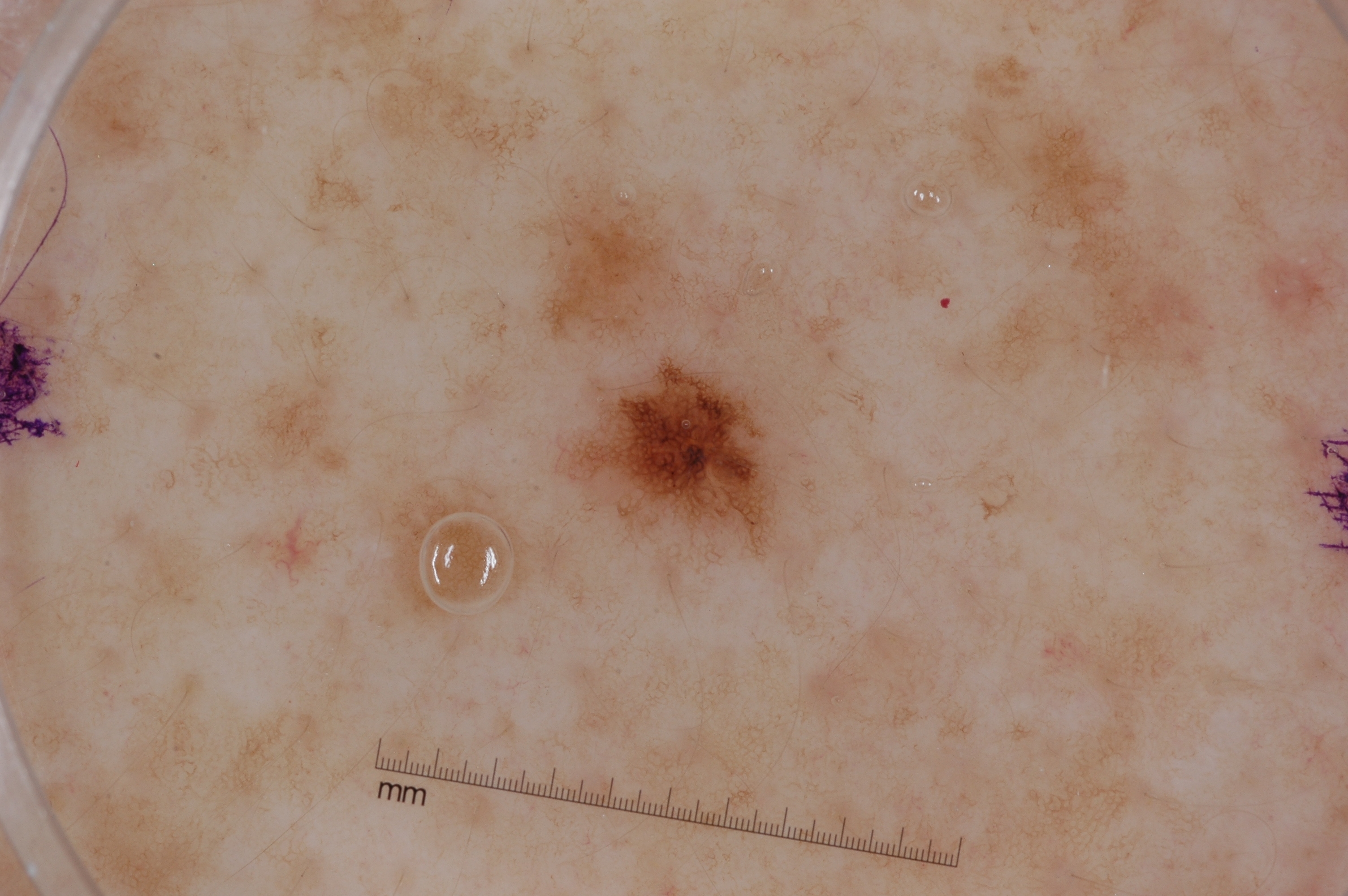Q: Who is the patient?
A: female, roughly 55 years of age
Q: What is the imaging modality?
A: dermoscopy
Q: What dermoscopic features are present?
A: pigment network; absent: milia-like cysts, negative network, and streaks
Q: Where is the lesion located?
A: x1=553, y1=352, x2=786, y2=578
Q: Lesion extent?
A: ~3% of the field
Q: What is this lesion?
A: a melanocytic nevus, a benign lesion